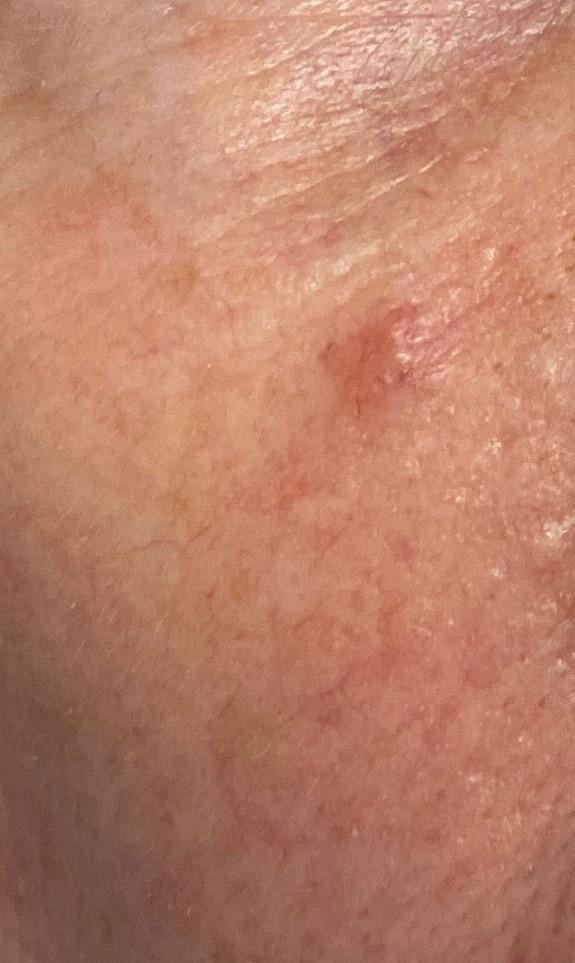A female subject about 70 years old. An overview clinical photograph of a skin lesion. The patient is Fitzpatrick phototype II. Located on the head or neck. Histopathologically confirmed as a malignant, adnexal lesion — a basal cell carcinoma.